A dermoscopy image of a single skin lesion.
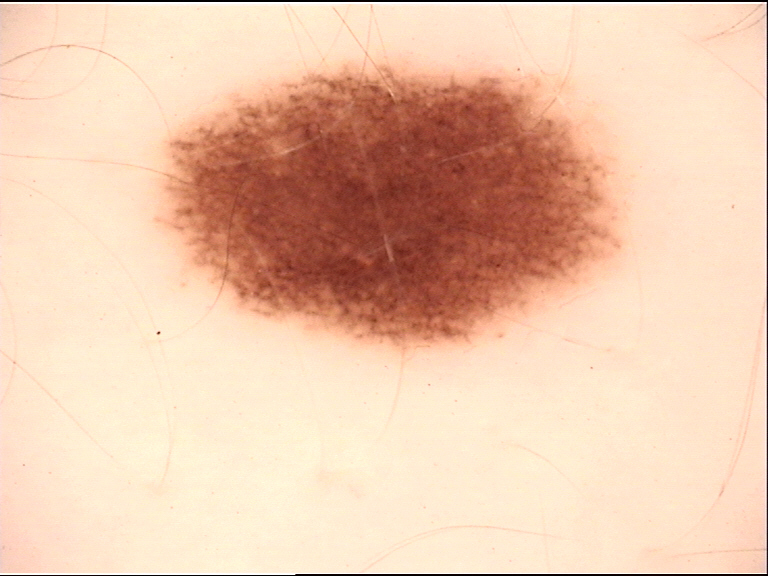Classified as a dysplastic junctional nevus.